A dermoscopic image of a skin lesion:
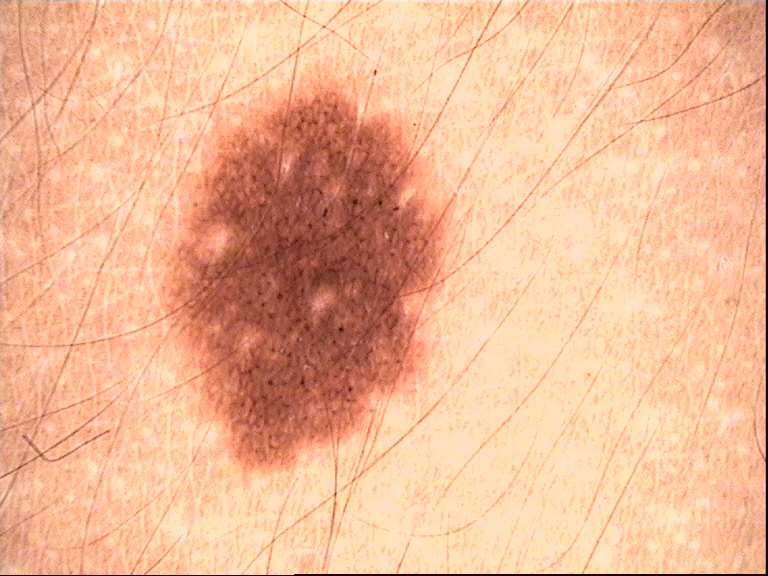label: dysplastic junctional nevus (expert consensus).